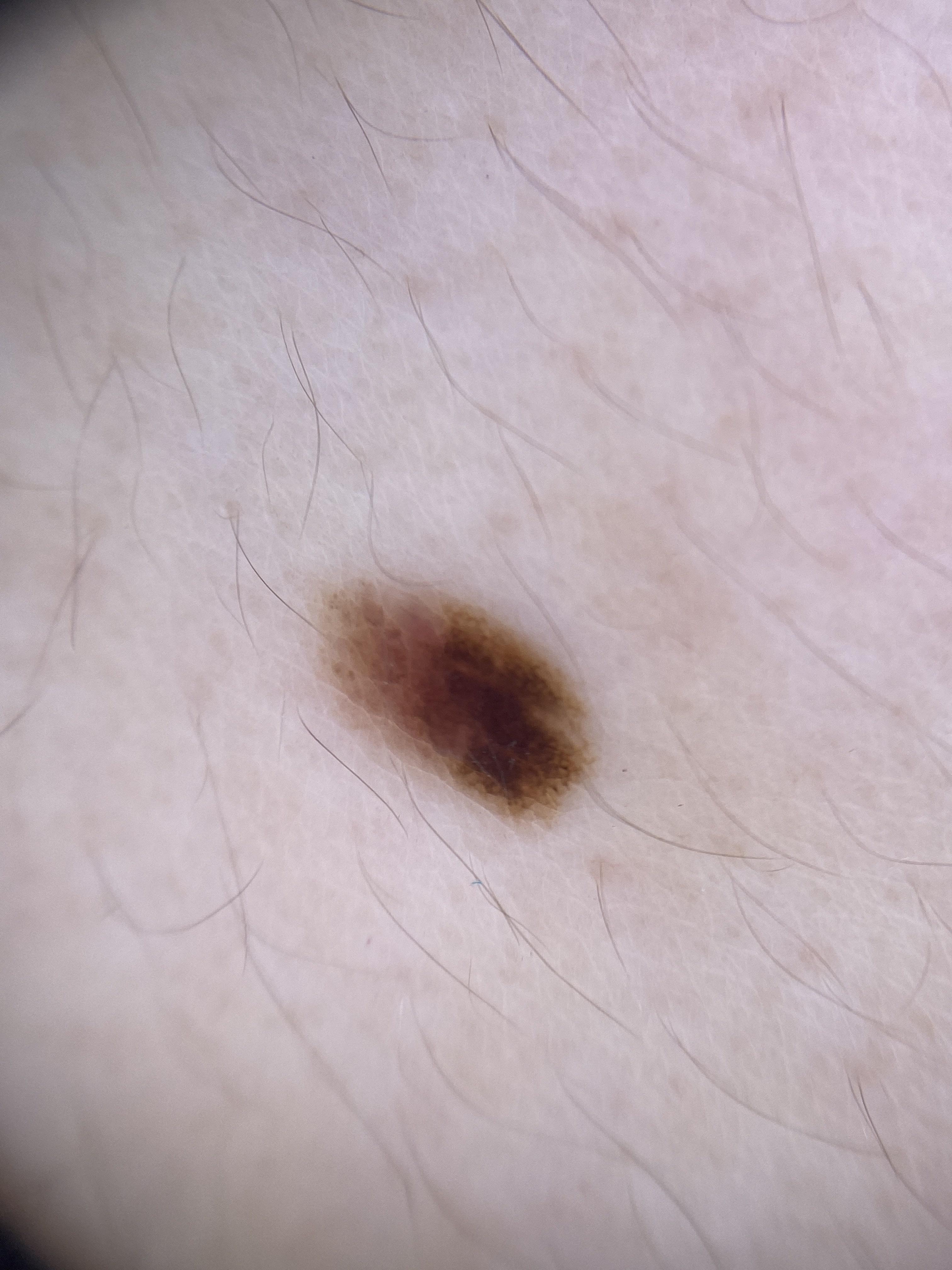Conclusion:
Clinically diagnosed as a nevus.